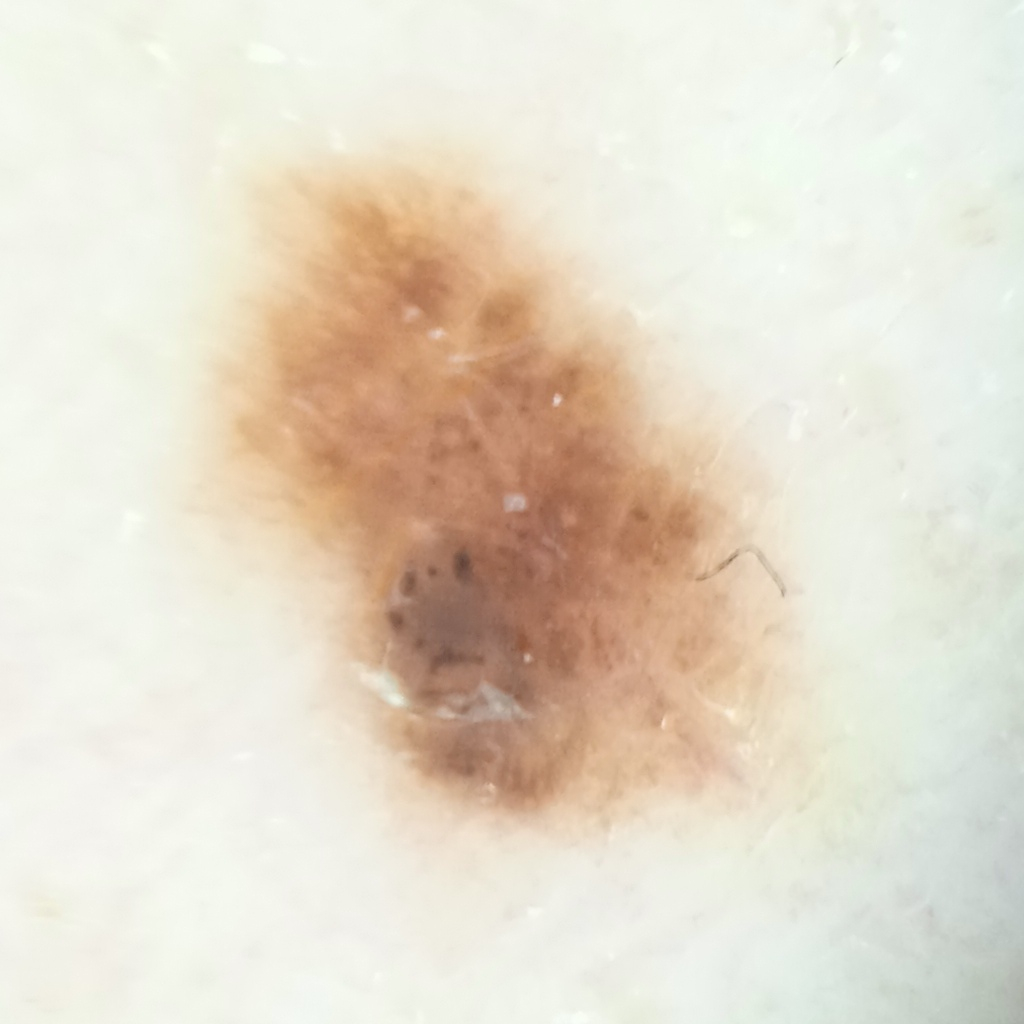risk factors = a personal history of skin cancer, a family history of skin cancer, a personal history of cancer; patient = male, 58 years of age; modality = dermoscopy; nevus count = numerous melanocytic nevi; clinical context = clinical suspicion of melanoma; lesion size = 5.2 mm; diagnostic label = melanocytic nevus (biopsy-proven).